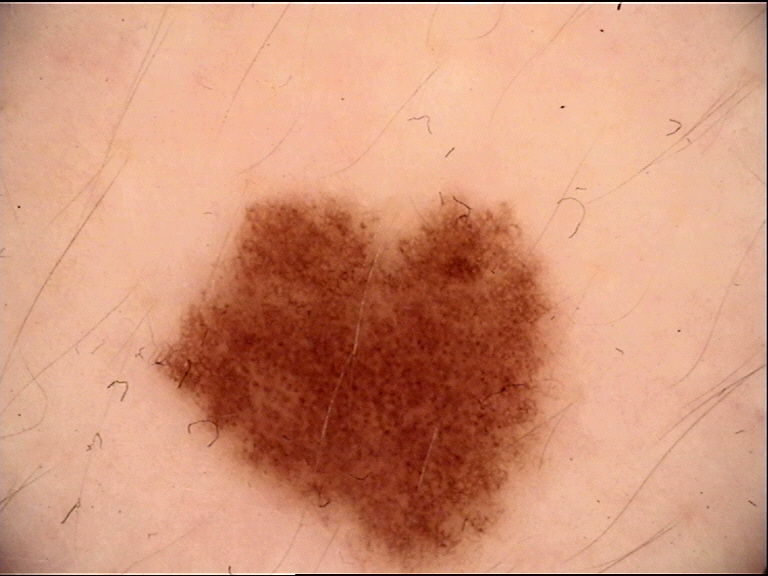<case>
<diagnosis>
<name>dysplastic junctional nevus</name>
<code>jd</code>
<malignancy>benign</malignancy>
<super_class>melanocytic</super_class>
<confirmation>expert consensus</confirmation>
</diagnosis>
</case>